The lesion involves the arm, the patient indicates the condition has been present for one to four weeks, texture is reported as raised or bumpy, this is a close-up image, the contributor is a female aged 18–29, lay graders estimated Monk skin tone scale 1 or 2 (two reviewer pools).
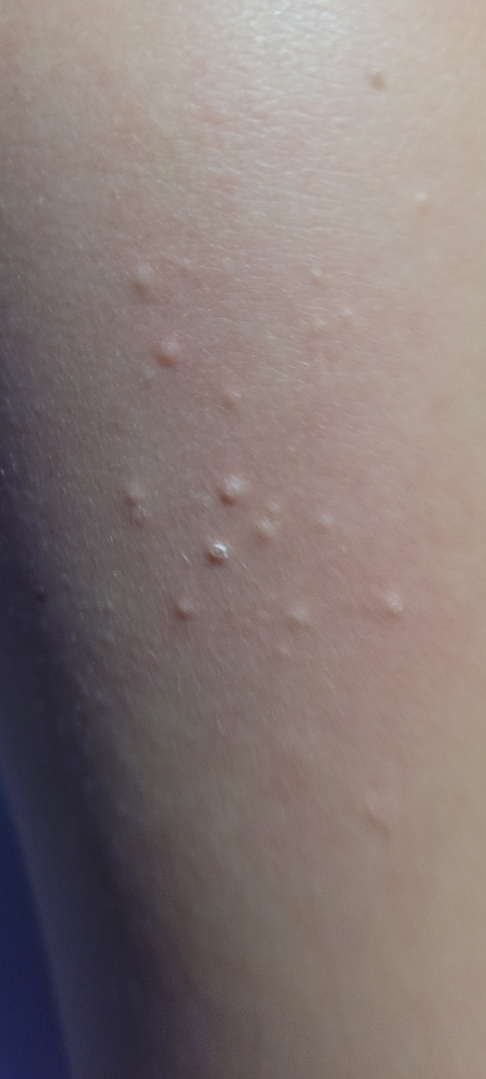assessment = not assessable.